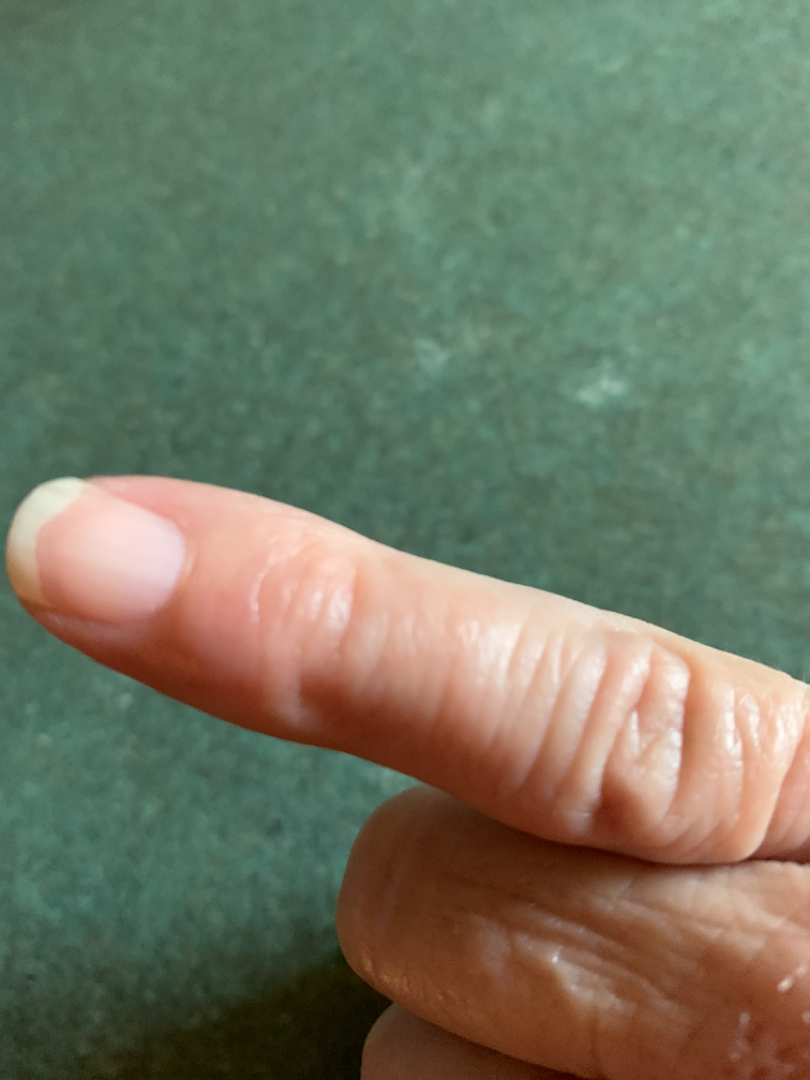The dermatologist found no clearly identifiable skin pathology in the image.
Close-up view.
The patient considered this a rash.
Present for less than one week.